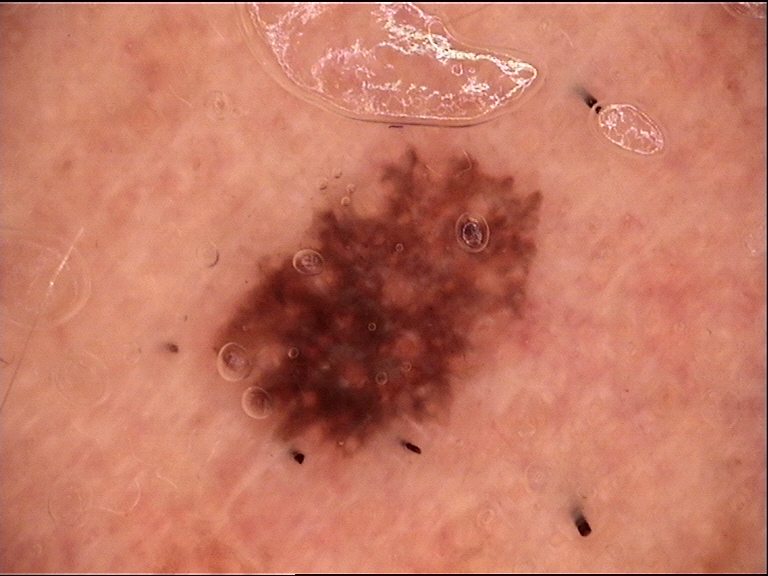assessment = dysplastic compound nevus (expert consensus).